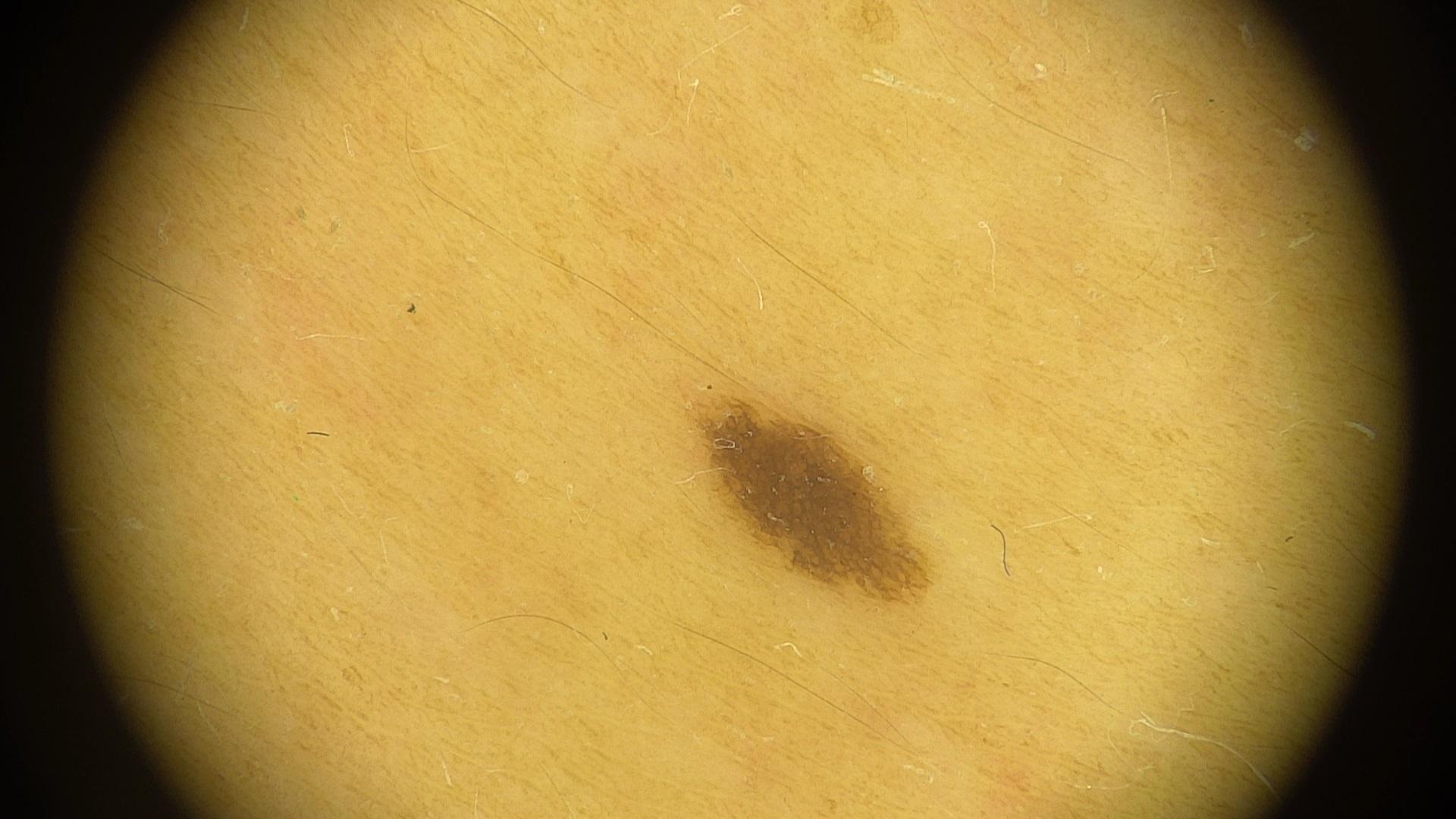Recorded as FST II.
A female subject aged approximately 35.
A dermoscopic image of a skin lesion.
Expert review favored a nevus.